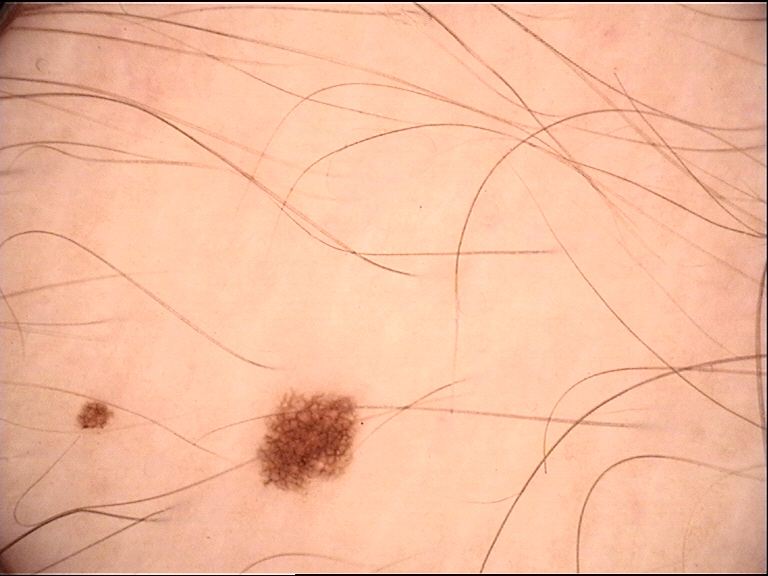modality: dermoscopy, label: dysplastic junctional nevus (expert consensus).